A dermoscopic close-up of a skin lesion:
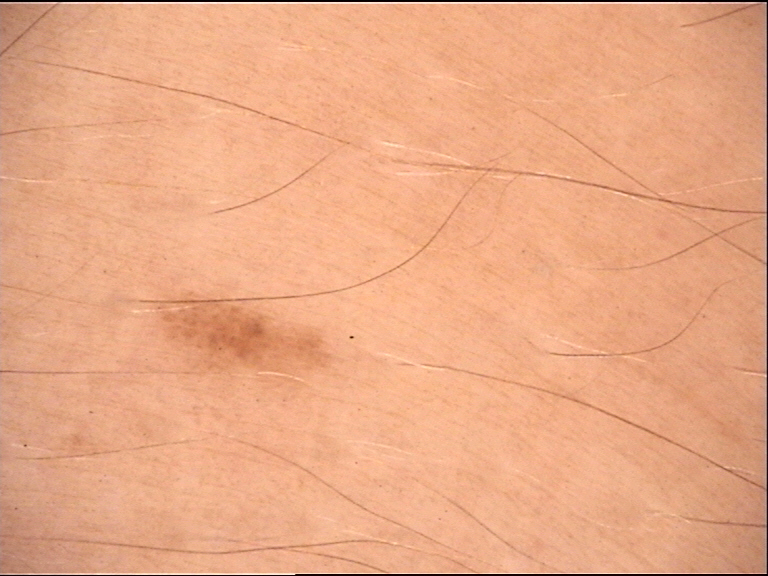Diagnosed as a dysplastic junctional nevus.